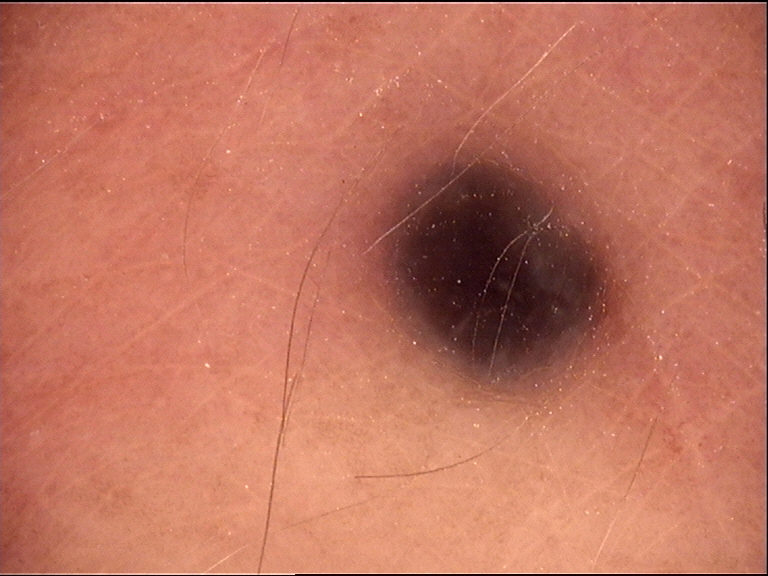A dermoscopic photograph of a skin lesion.
The diagnosis was a dermal lesion — a blue nevus.